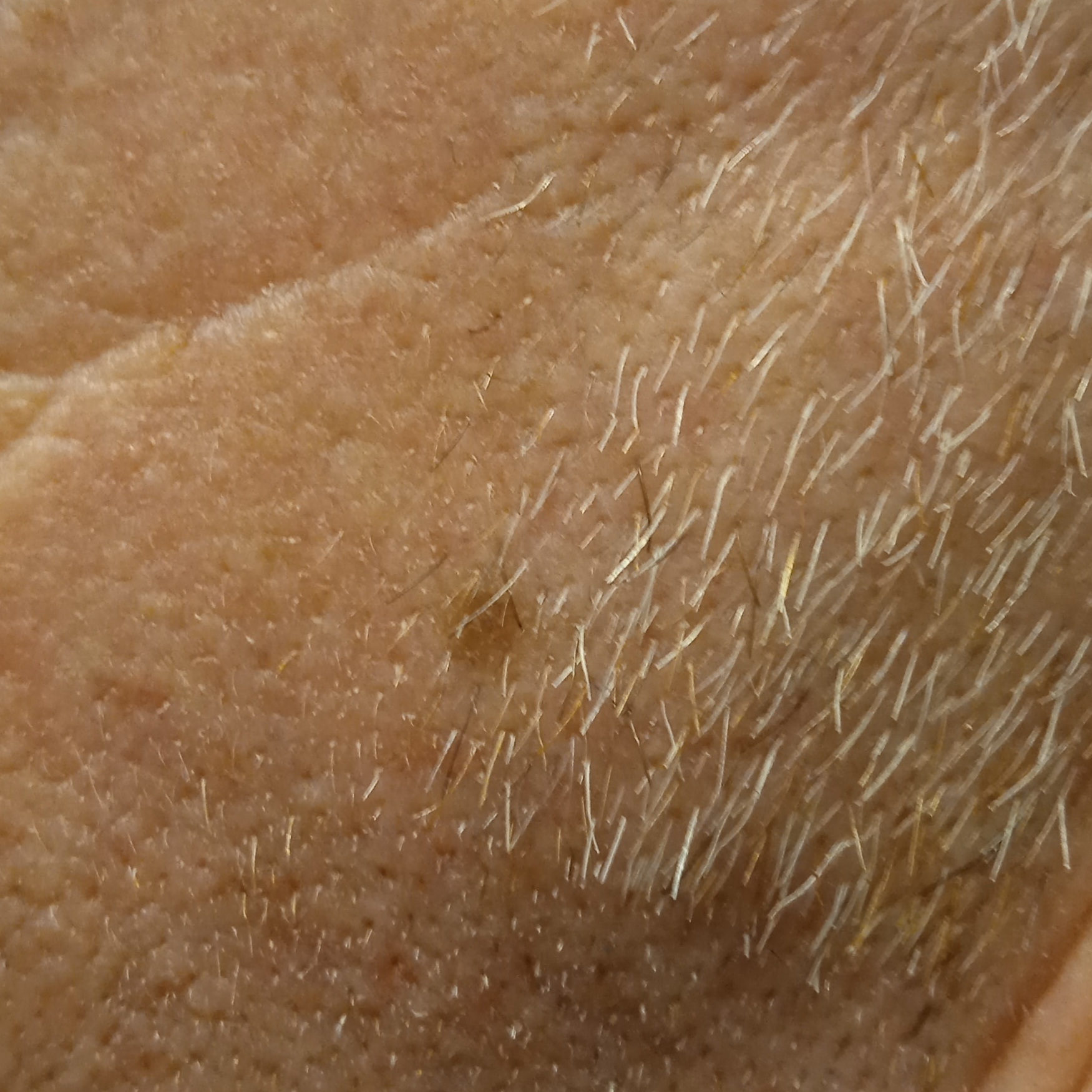Q: What kind of image is this?
A: clinical photo
Q: What is the patient's nevus burden?
A: few melanocytic nevi overall
Q: Tell me about the patient.
A: male, 66 years of age
Q: Why was this imaged?
A: research study (no referral diagnosis)
Q: Where is the lesion?
A: the face
Q: How large is the lesion?
A: 3.7 mm
Q: What was the diagnosis?
A: melanocytic nevus (dermatologist consensus)